A dermoscopic photograph of a skin lesion.
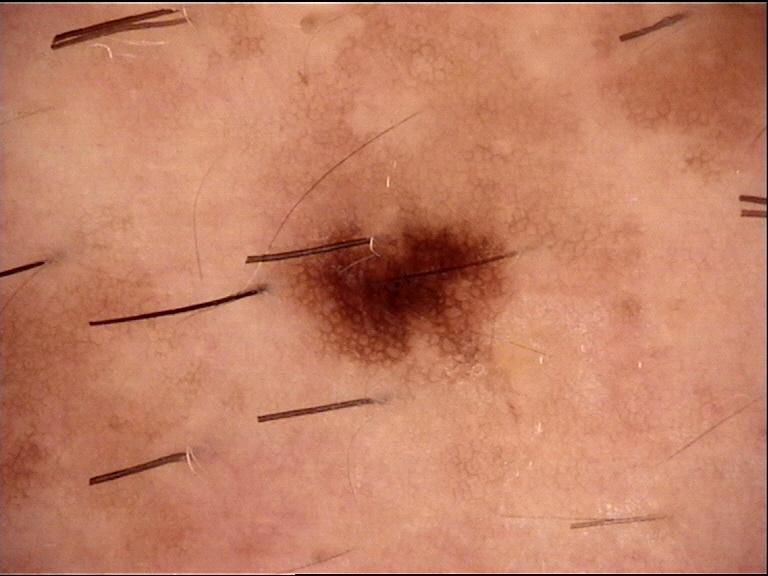diagnosis = dysplastic junctional nevus (expert consensus).